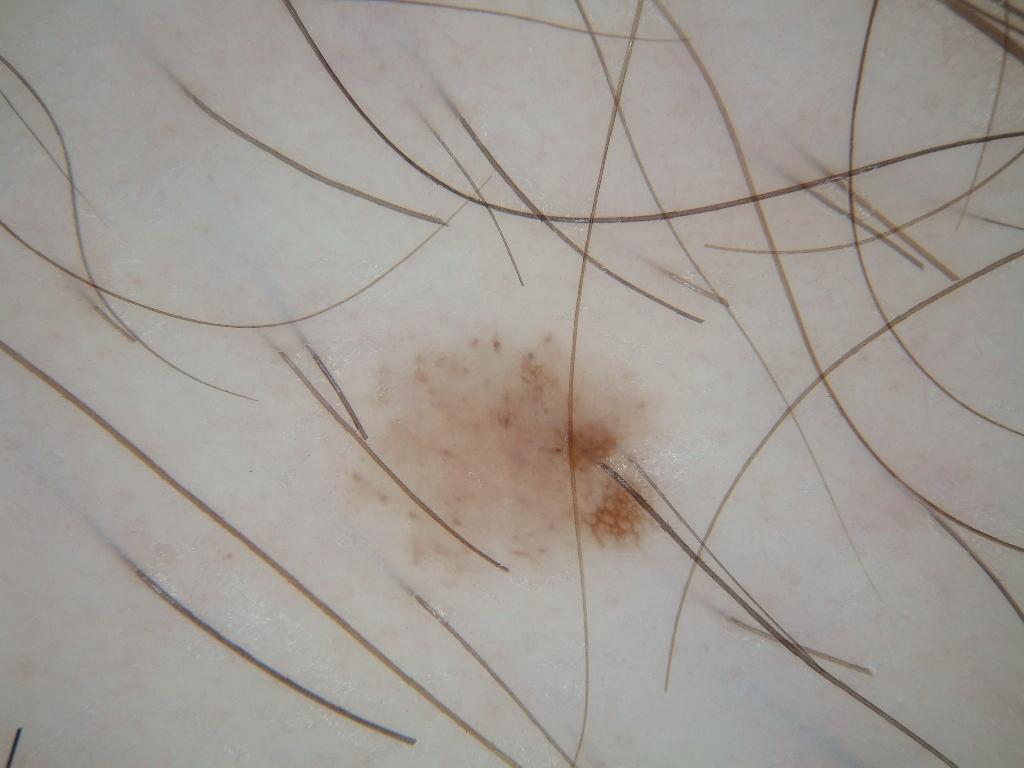modality — dermoscopic image
bounding box — 305/312/685/613
dermoscopic findings — globules and pigment network; absent: milia-like cysts, streaks, and negative network
impression — a melanocytic nevus